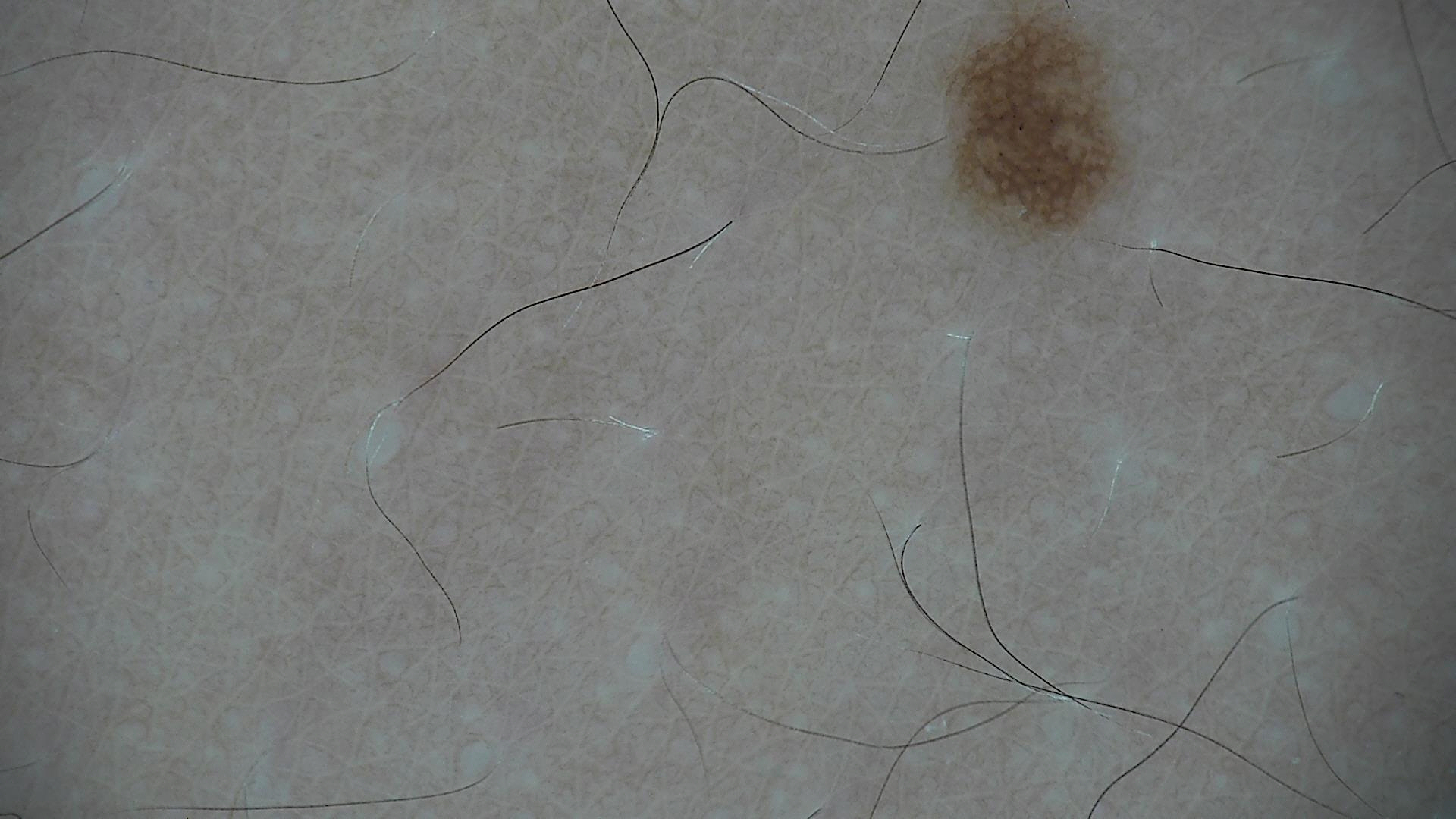The diagnostic label was a dysplastic junctional nevus.